A clinical close-up photograph of a skin lesion. A patient aged 50.
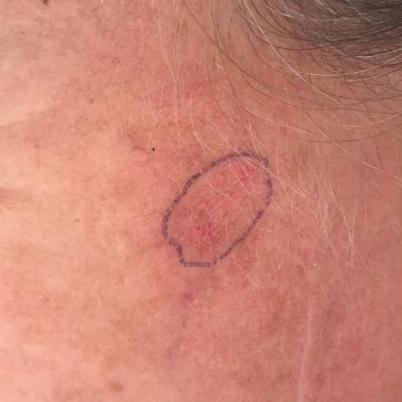The lesion is on the face. Per patient report, the lesion itches. The diagnostic impression was an actinic keratosis.